The subject is 18–29, female. Located on the head or neck. Close-up view: 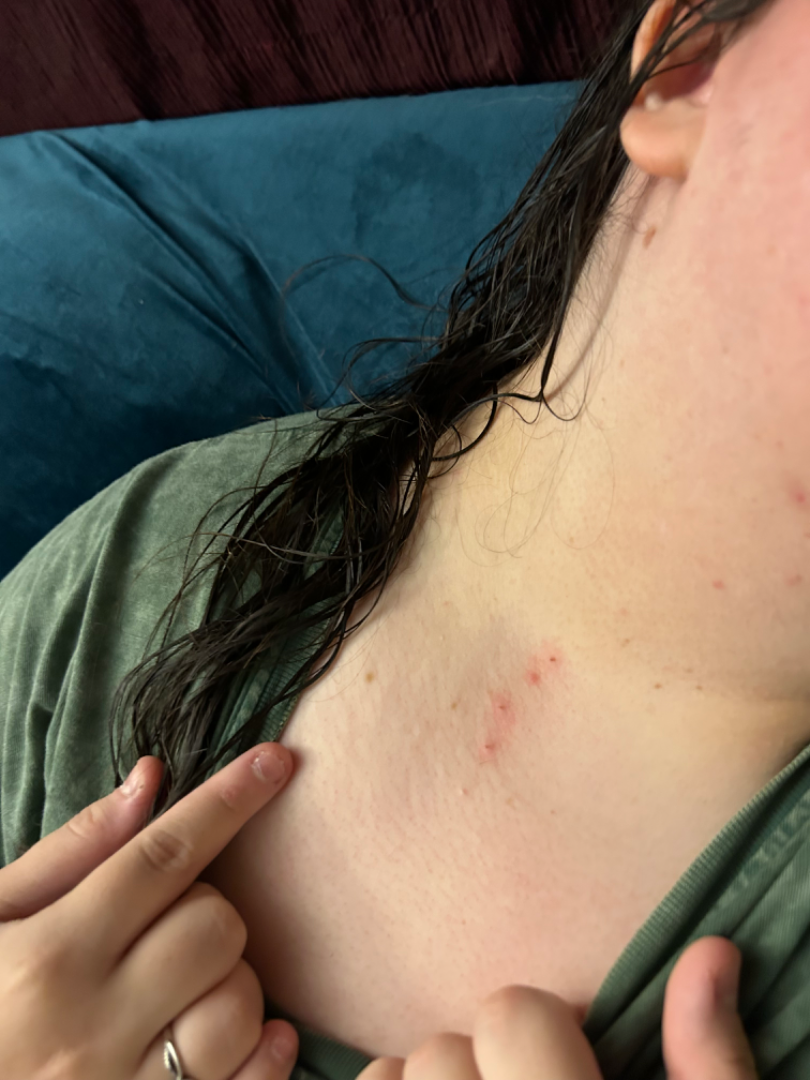Case summary:
- patient's own categorization: a rash
- texture: fluid-filled and raised or bumpy
- reported symptoms: itching
- present for: less than one week
- constitutional symptoms: fatigue
- assessment: Insect Bite and Herpes Simplex were considered with similar weight